Dermoscopy of a skin lesion:
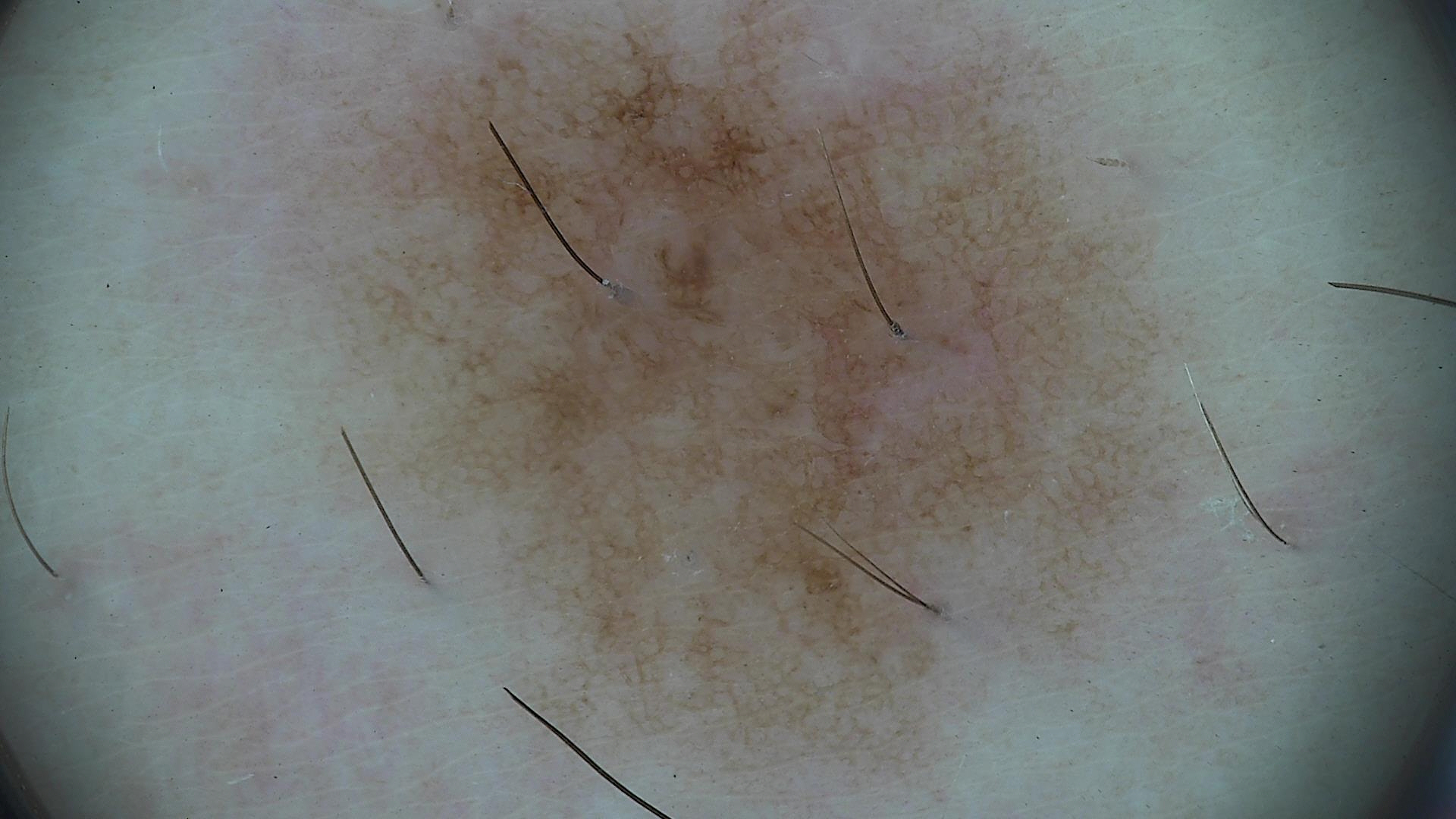Diagnosed as a benign lesion — a dysplastic junctional nevus.